A male patient aged around 70.
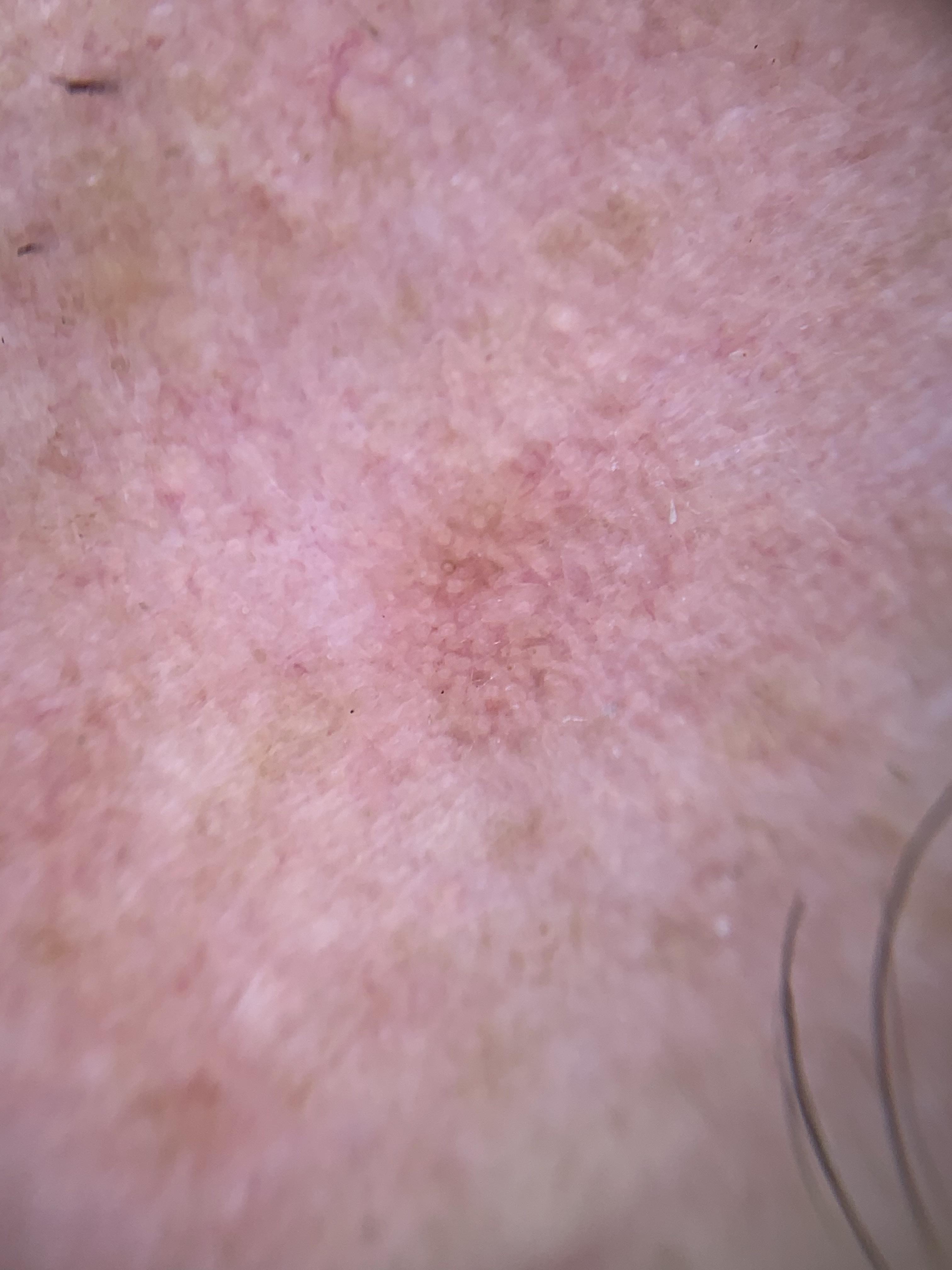{"diagnosis": {"name": "Solar or actinic keratosis", "malignancy": "indeterminate", "confirmation": "expert clinical impression", "lineage": "epidermal"}}